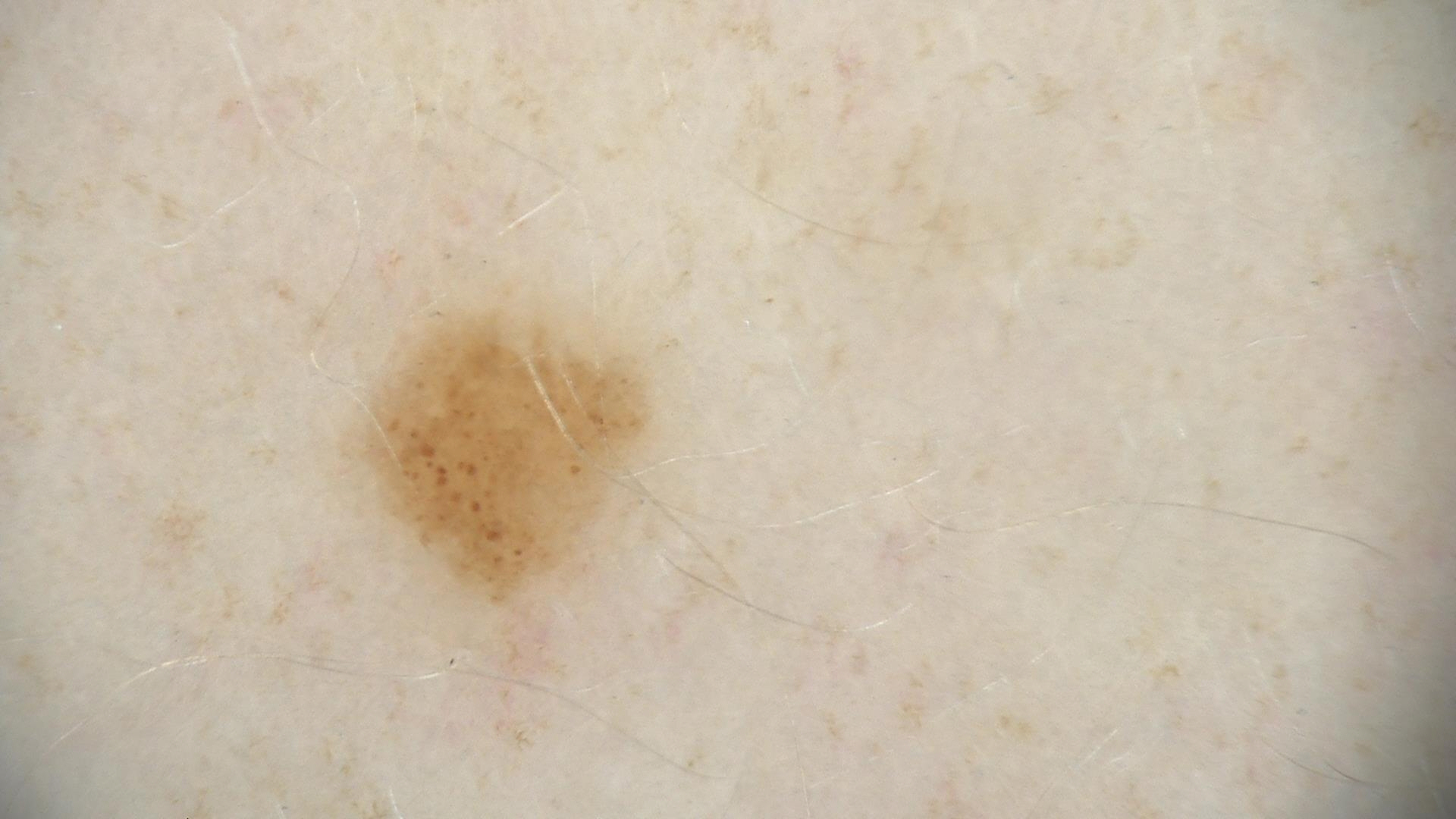Q: What is the imaging modality?
A: dermoscopy
Q: What was the diagnostic impression?
A: dysplastic junctional nevus (expert consensus)